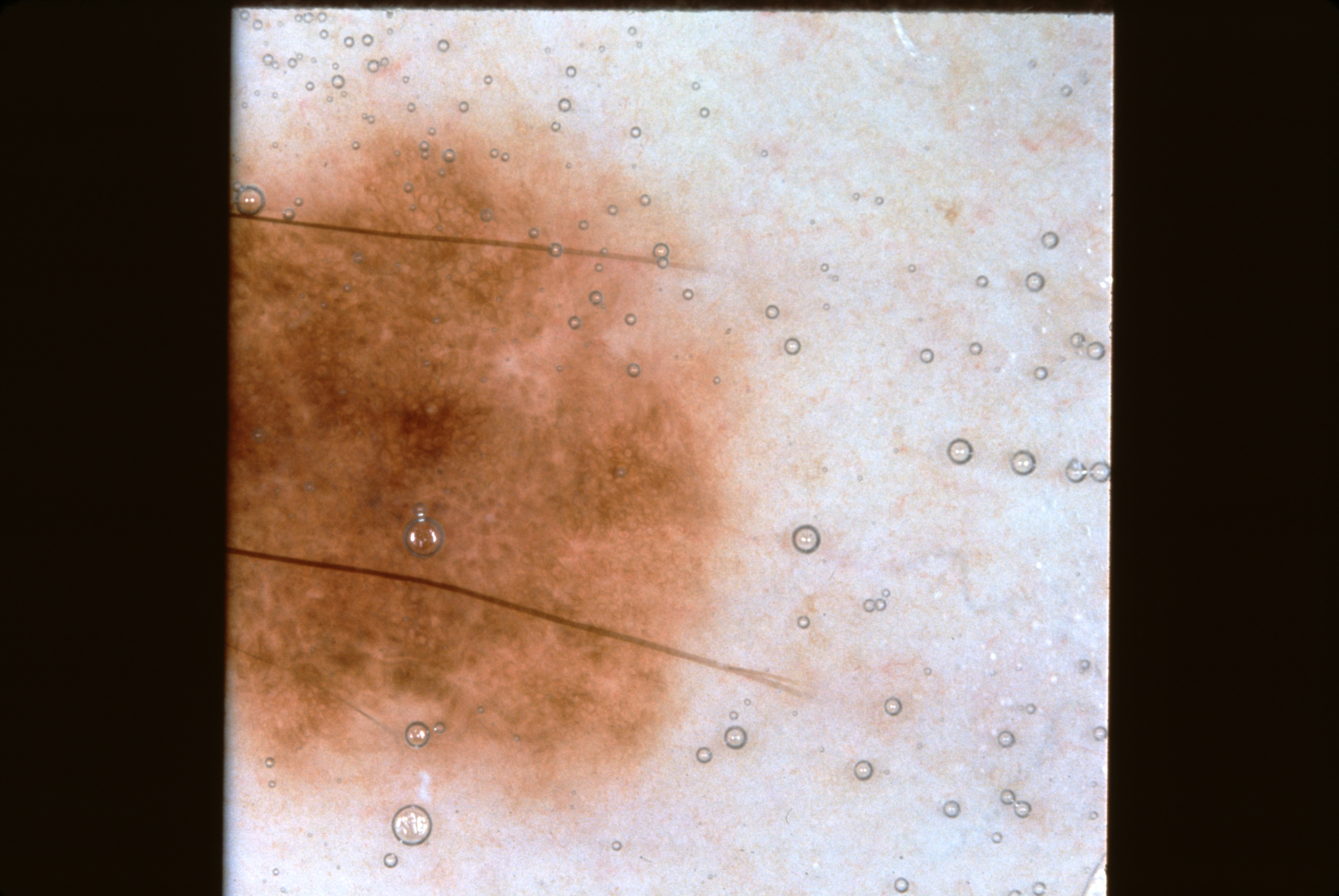A female subject aged around 40. A dermoscopy image of a single skin lesion. As (left, top, right, bottom), the lesion's extent is [224,79,793,851]. On dermoscopy, the lesion shows pigment network and negative network. The lesion takes up about 31% of the image. Expert review diagnosed this as a melanocytic nevus, a benign lesion.